Symptoms reported: itching and bothersome appearance · the subject is male · an image taken at an angle · the affected area is the arm · self-categorized by the patient as a rash · the patient reported no systemic symptoms: 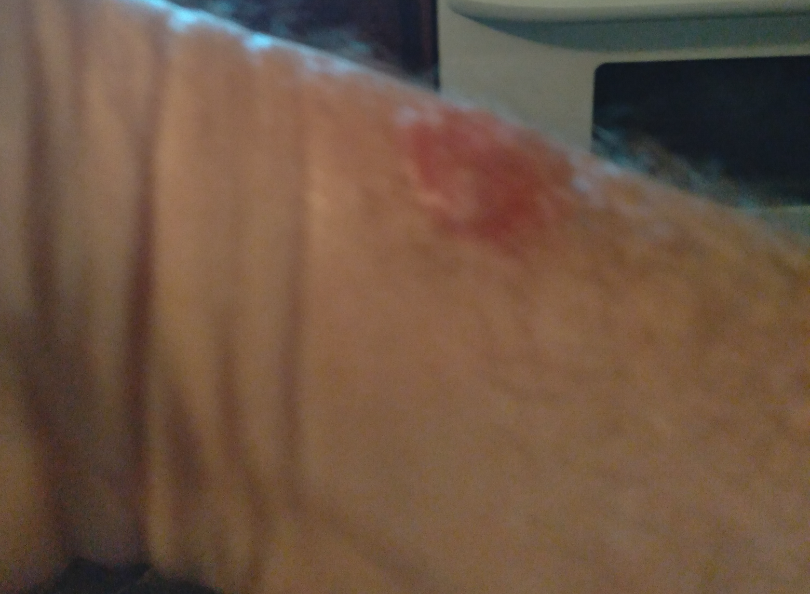assessment: indeterminate